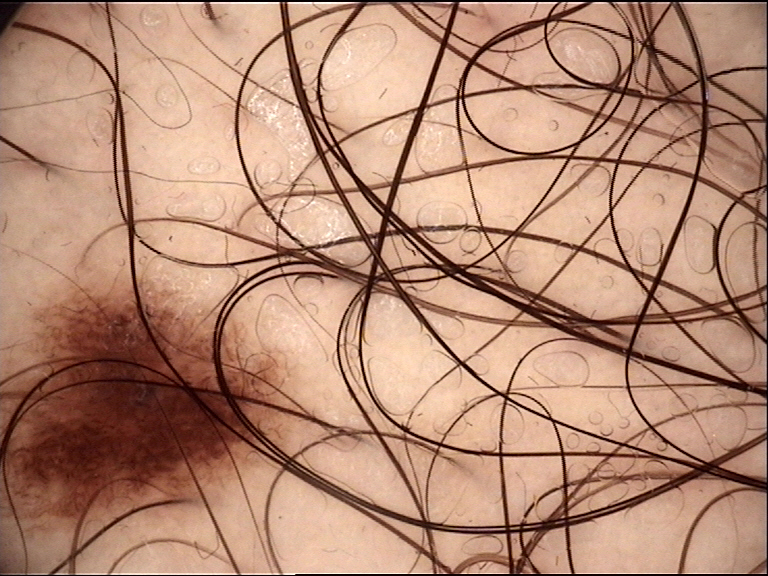Consistent with a junctional nevus.